An image taken at a distance · the affected area is the back of the hand.
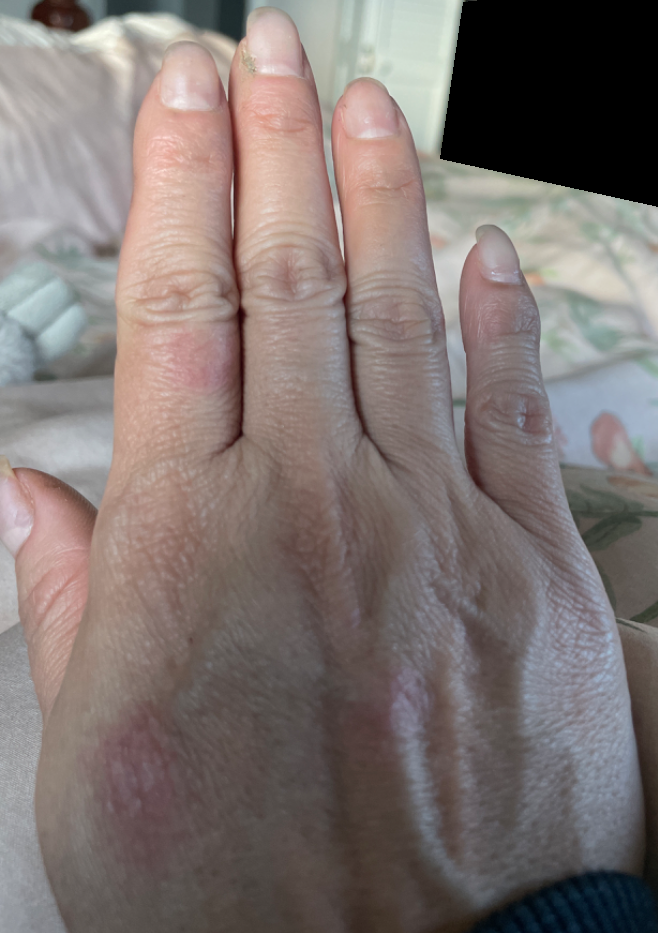Prurigo nodularis and Eczema were each considered, in no particular order; lower on the differential is Insect Bite; less likely is Lichen Simplex Chronicus; less probable is Keratosis.